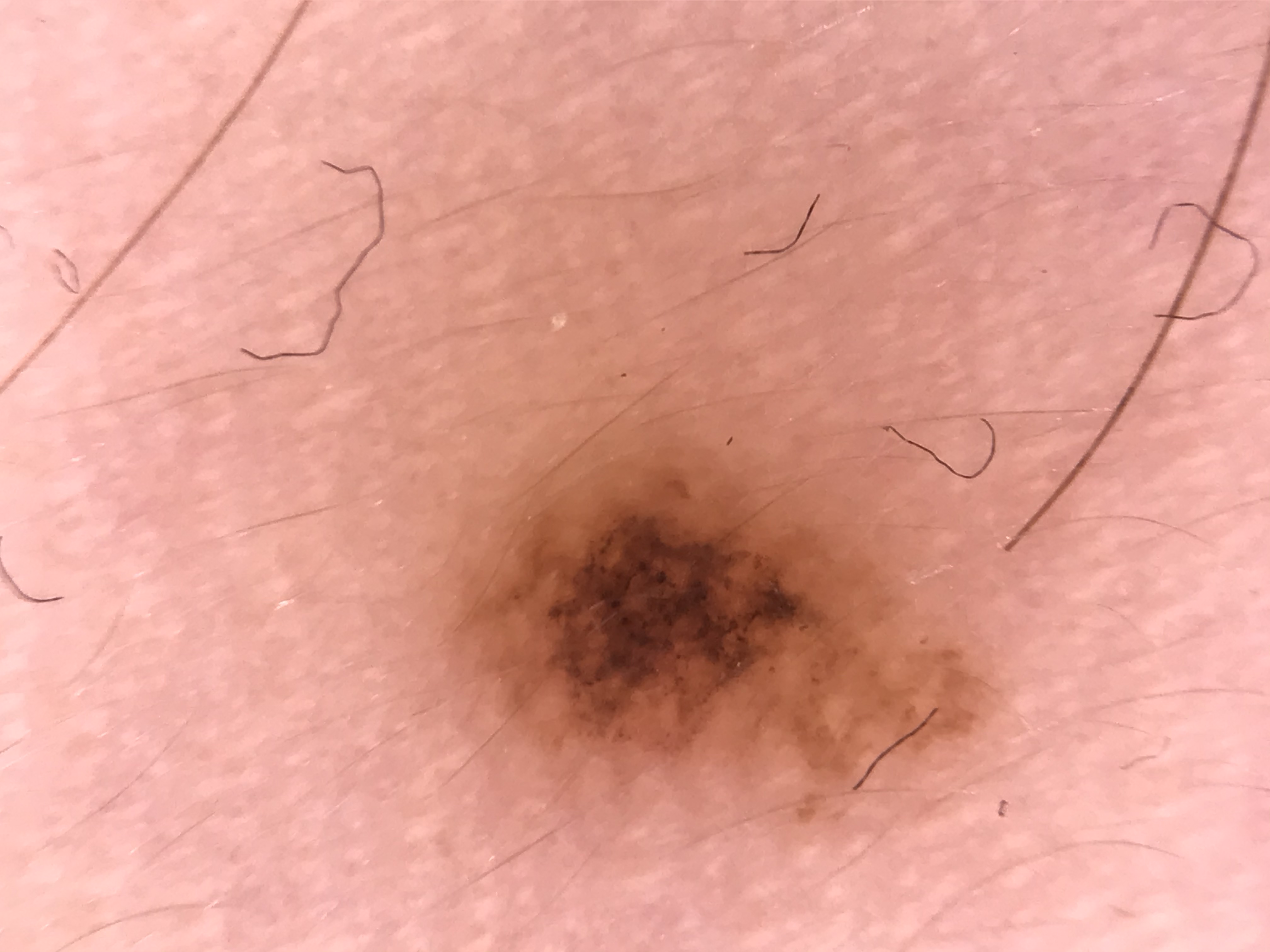* image · dermatoscopy
* assessment · compound nevus (expert consensus)